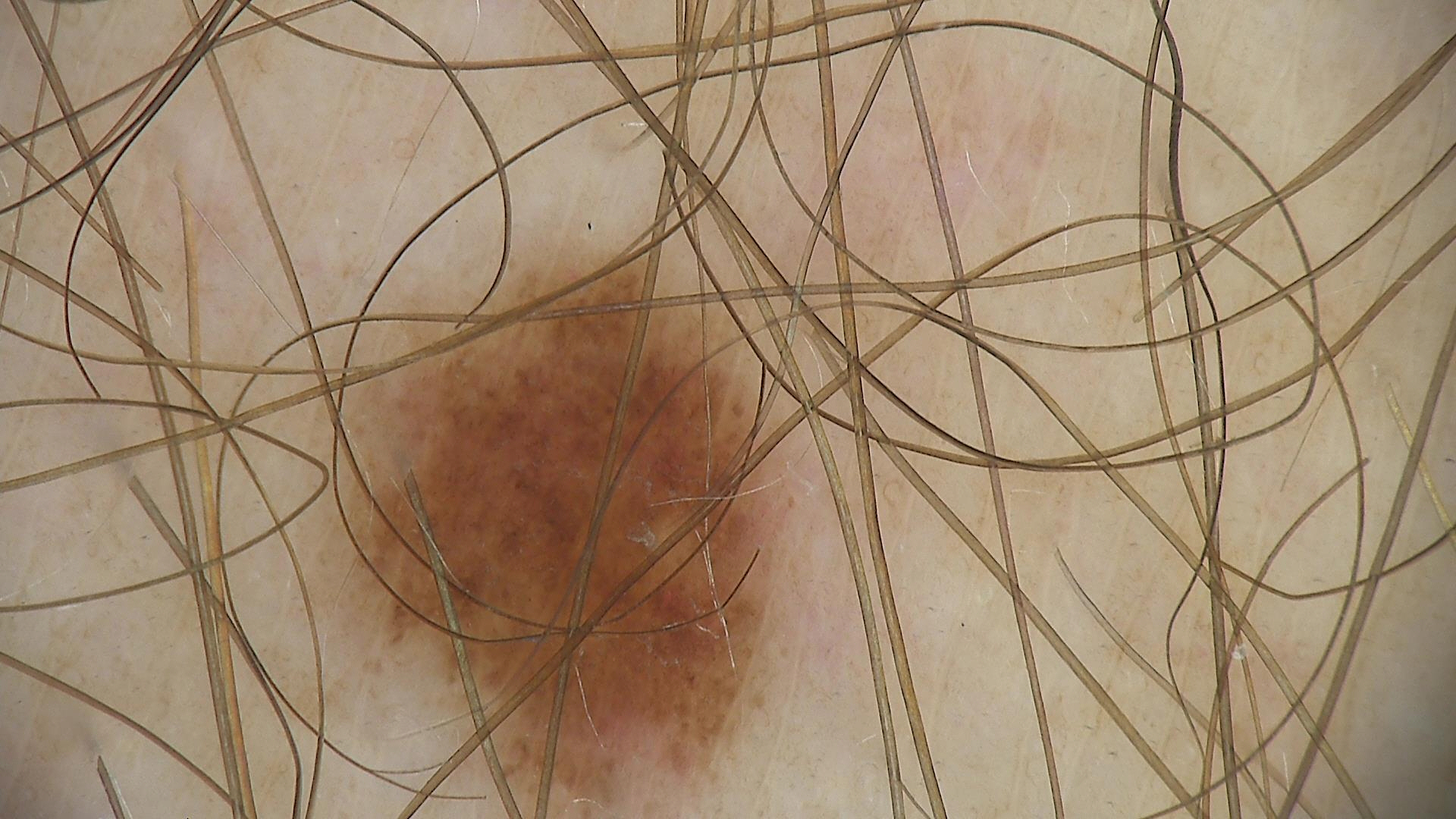Conclusion: The diagnostic label was a dysplastic junctional nevus.